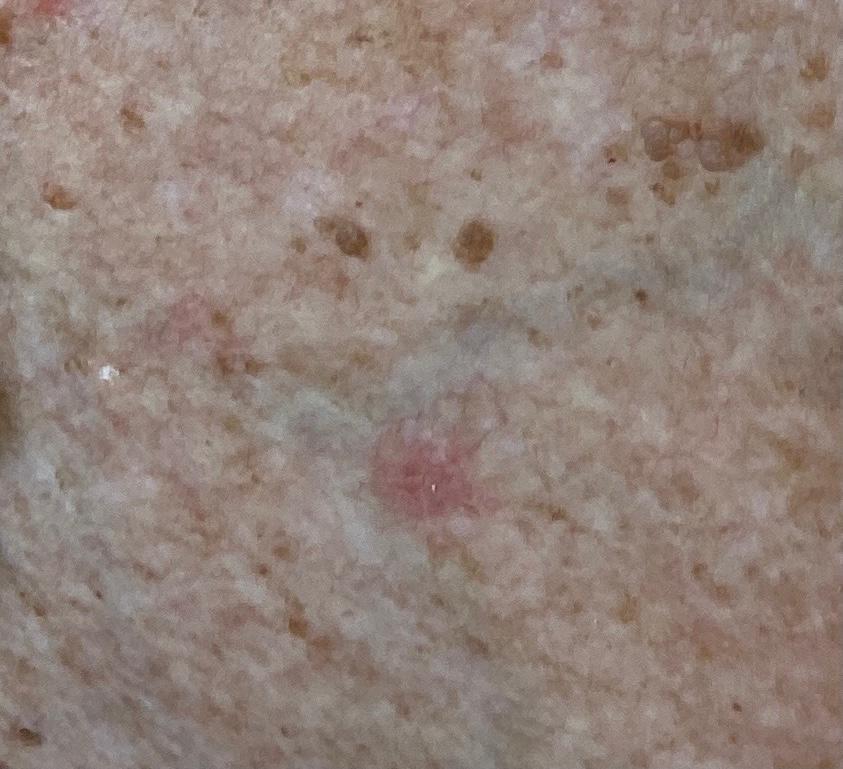patient:
  age_approx: 70
  sex: female
image: clinical photograph
diagnosis:
  name: Basal cell carcinoma
  malignancy: malignant
  confirmation: histopathology
  lineage: adnexal